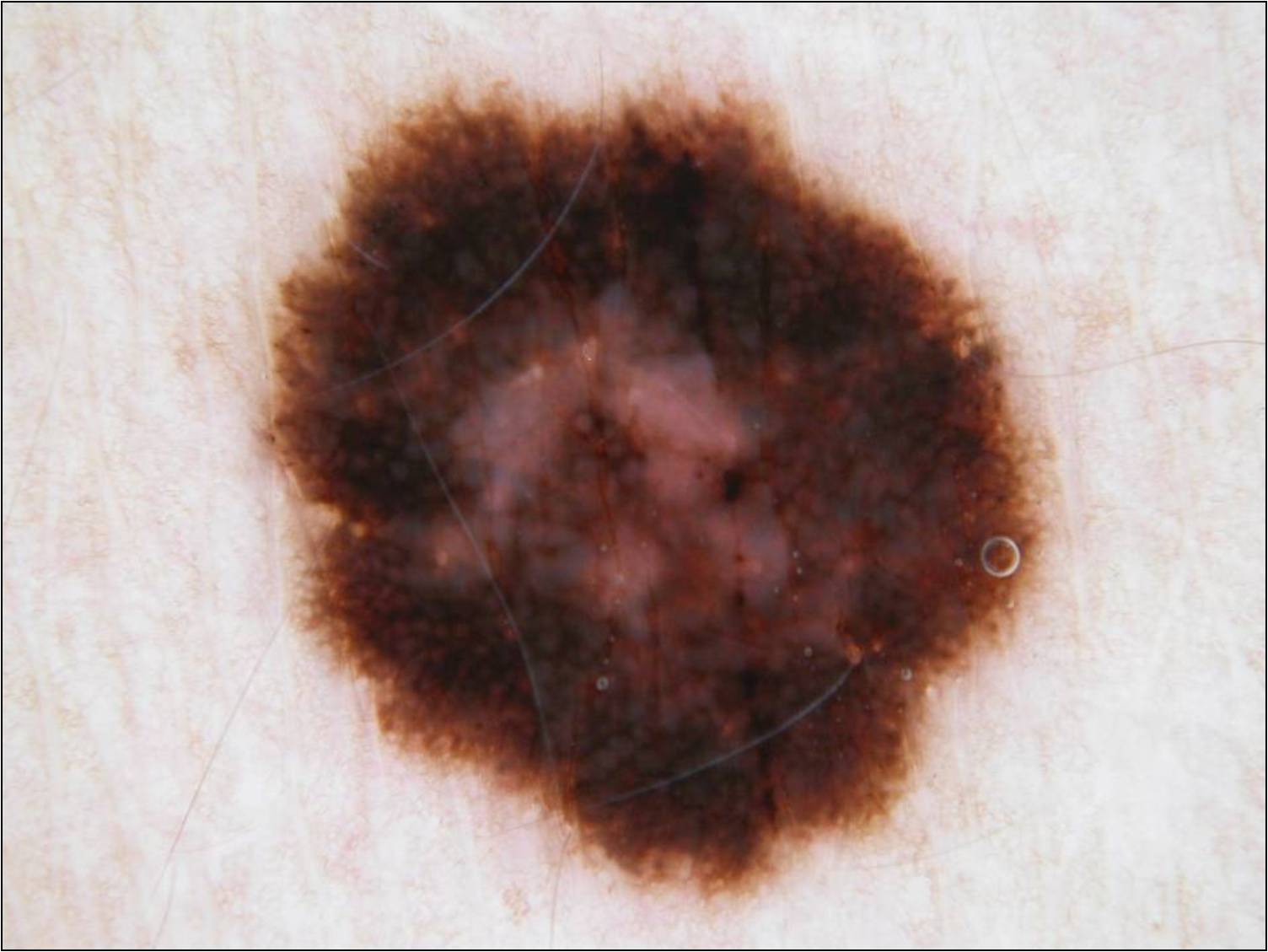  image:
    modality: dermoscopy
  lesion_location:
    bbox_xyxy:
      - 254
      - 86
      - 1045
      - 896
  diagnosis:
    name: melanoma
    malignancy: malignant
    lineage: melanocytic
    provenance: histopathology